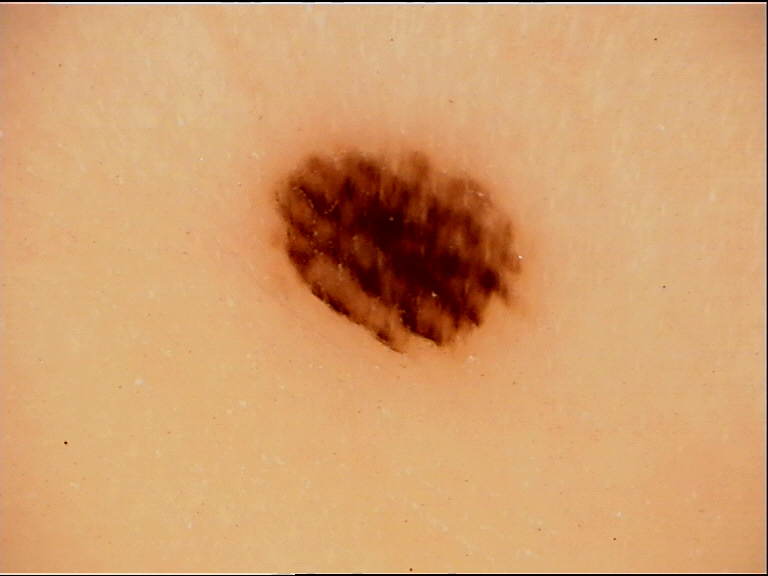Case:
A dermoscopy image of a single skin lesion. The architecture is that of a banal lesion.
Conclusion:
The diagnostic label was an acral junctional nevus.